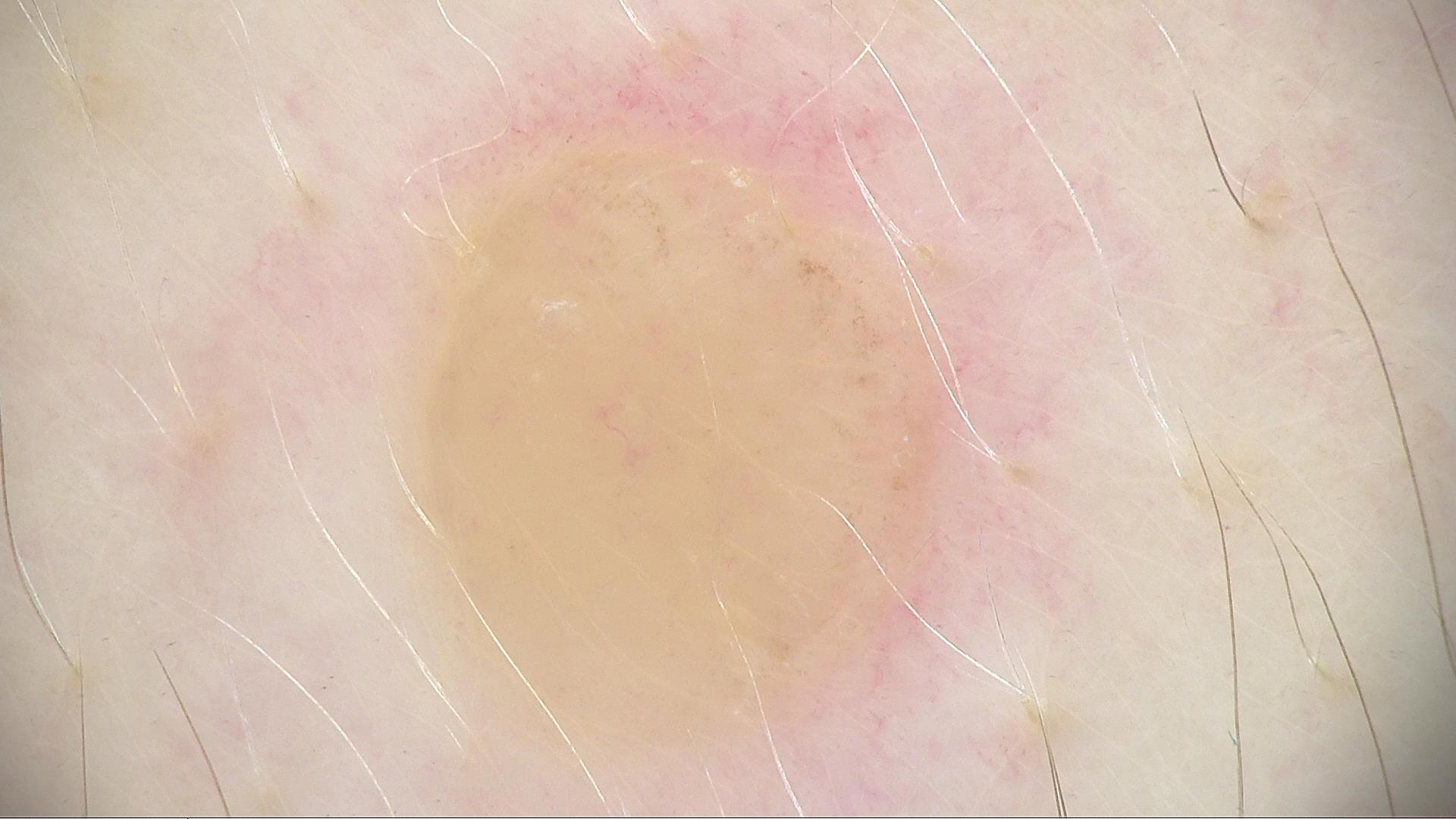A dermoscopic photograph of a skin lesion.
The diagnostic label was a banal lesion — a dermal nevus.